A dermoscopic close-up of a skin lesion.
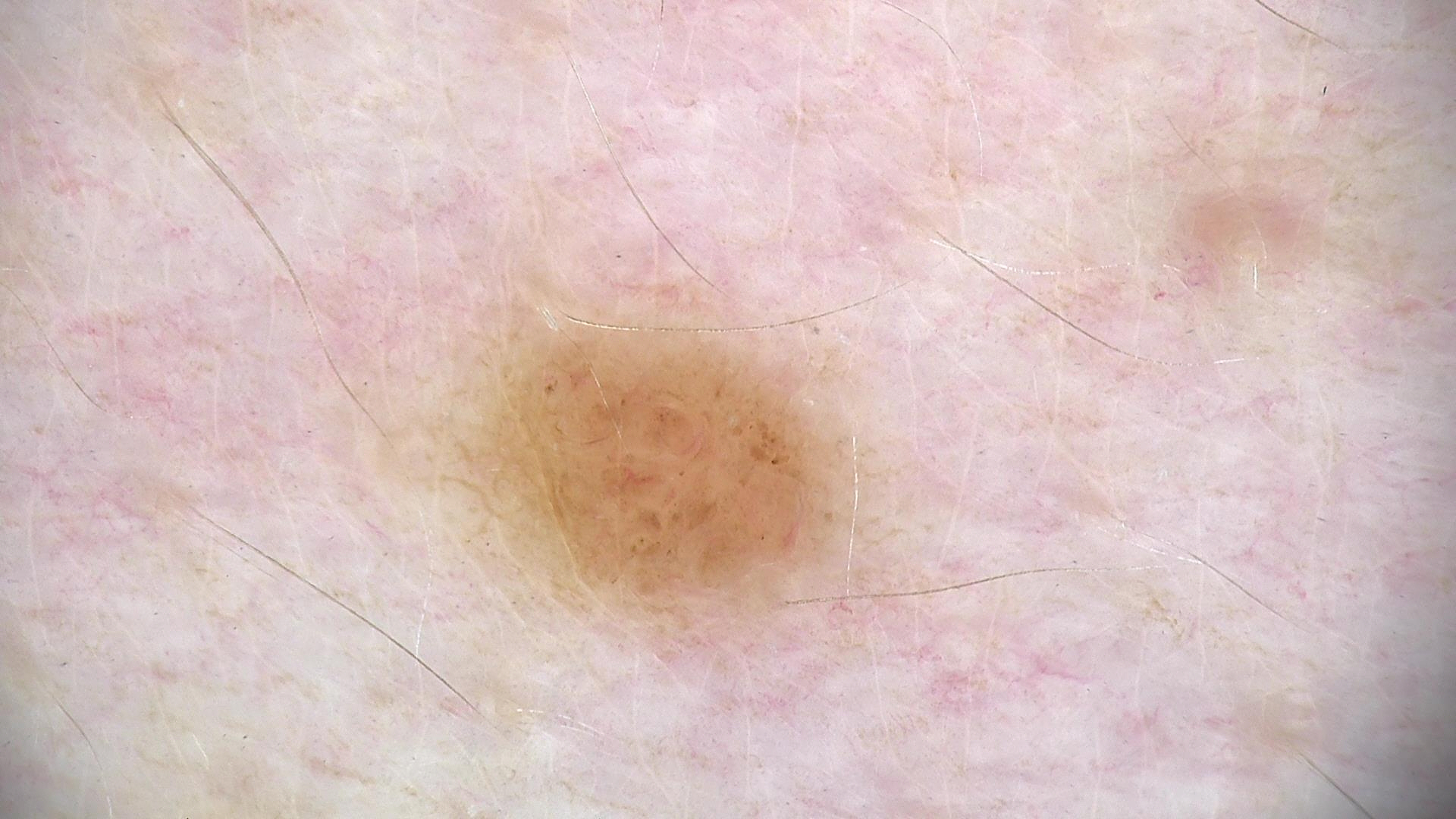assessment = dysplastic junctional nevus (expert consensus)